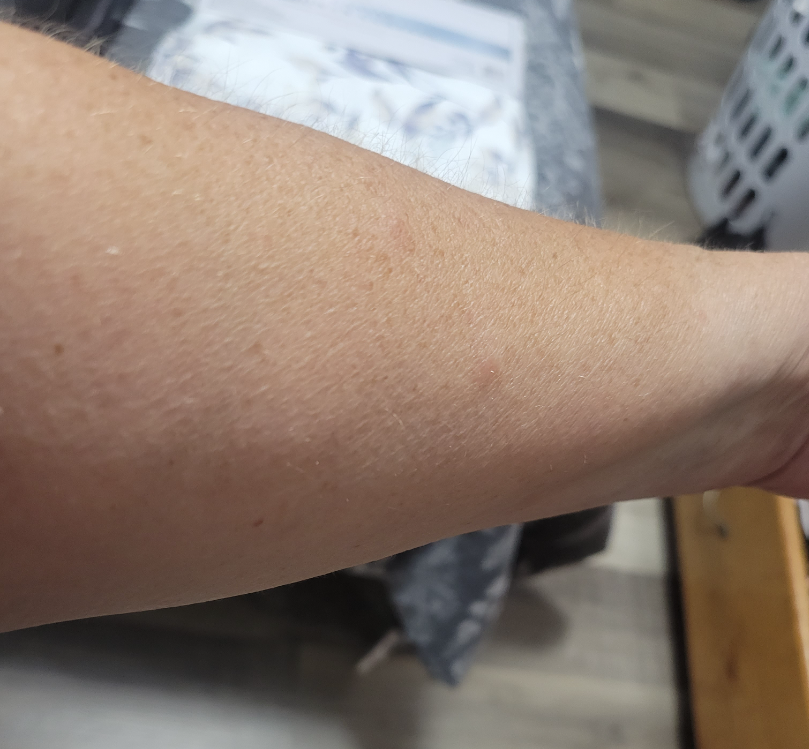assessment: unable to determine | history: less than one week | skin tone: Fitzpatrick III; lay graders estimated 3 on the Monk Skin Tone | framing: at an angle | described texture: raised or bumpy | reported symptoms: itching | site: arm.